A dermatoscopic image of a skin lesion: 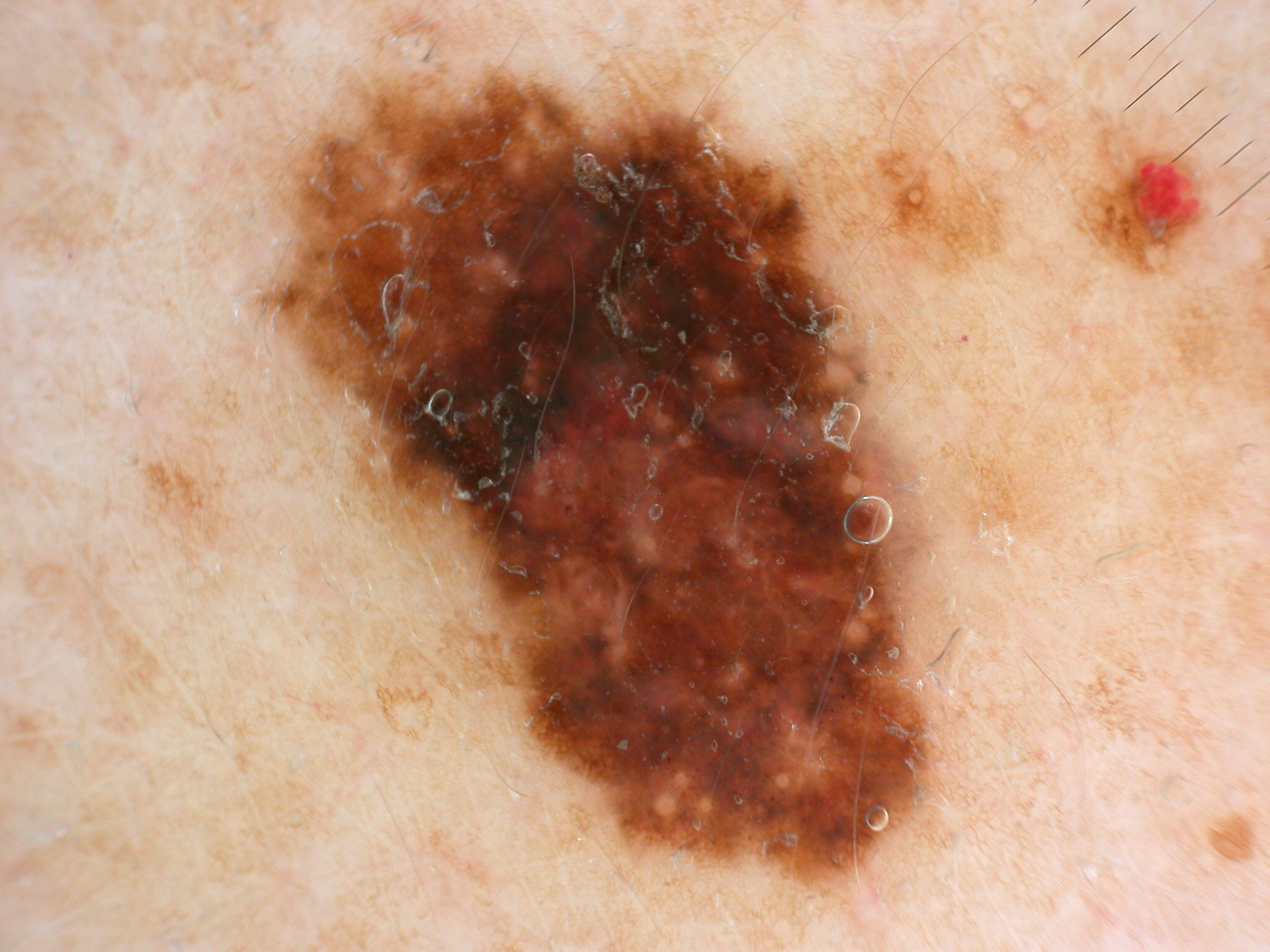The lesion occupies the region x1=252, y1=68, x2=956, y2=899. The dermoscopic pattern shows pigment network; no streaks, milia-like cysts, negative network, or globules. The lesion covers approximately 31% of the dermoscopic field. The biopsy diagnosis was a melanoma.